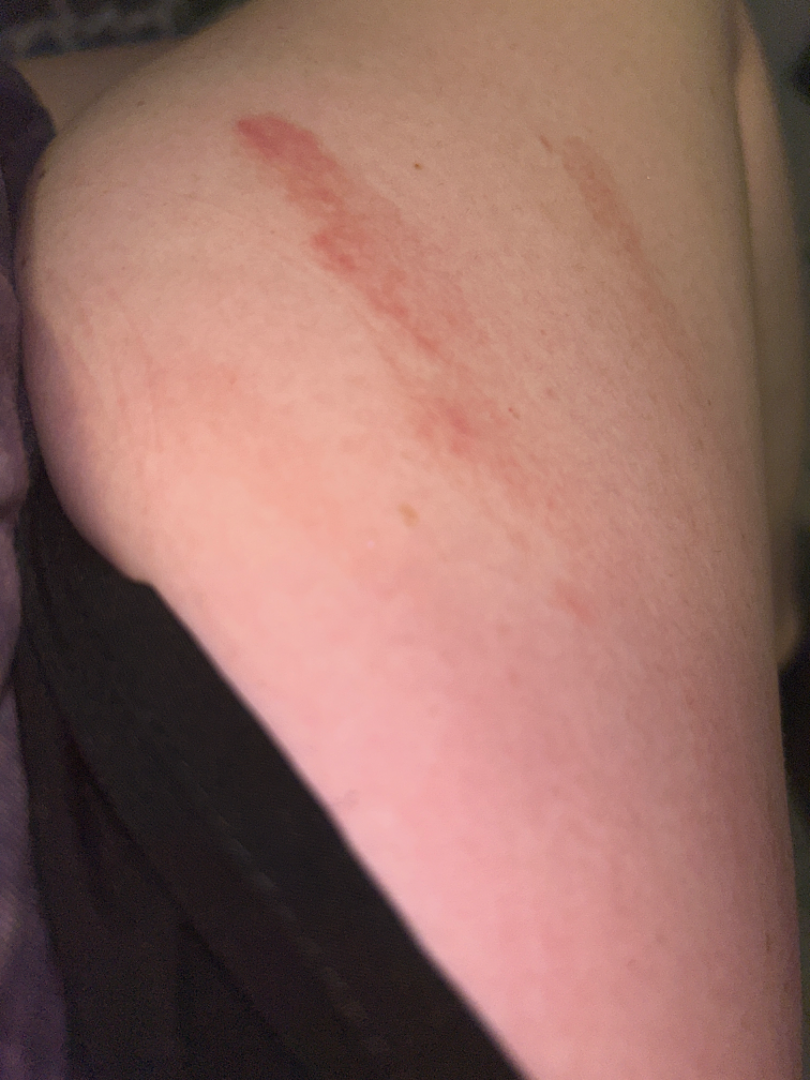assessment=could not be assessed; contributor=female, age 18–29; photo taken=at an angle; anatomic site=leg.